A male patient in their mid- to late 60s. A dermoscopic photograph of a skin lesion — 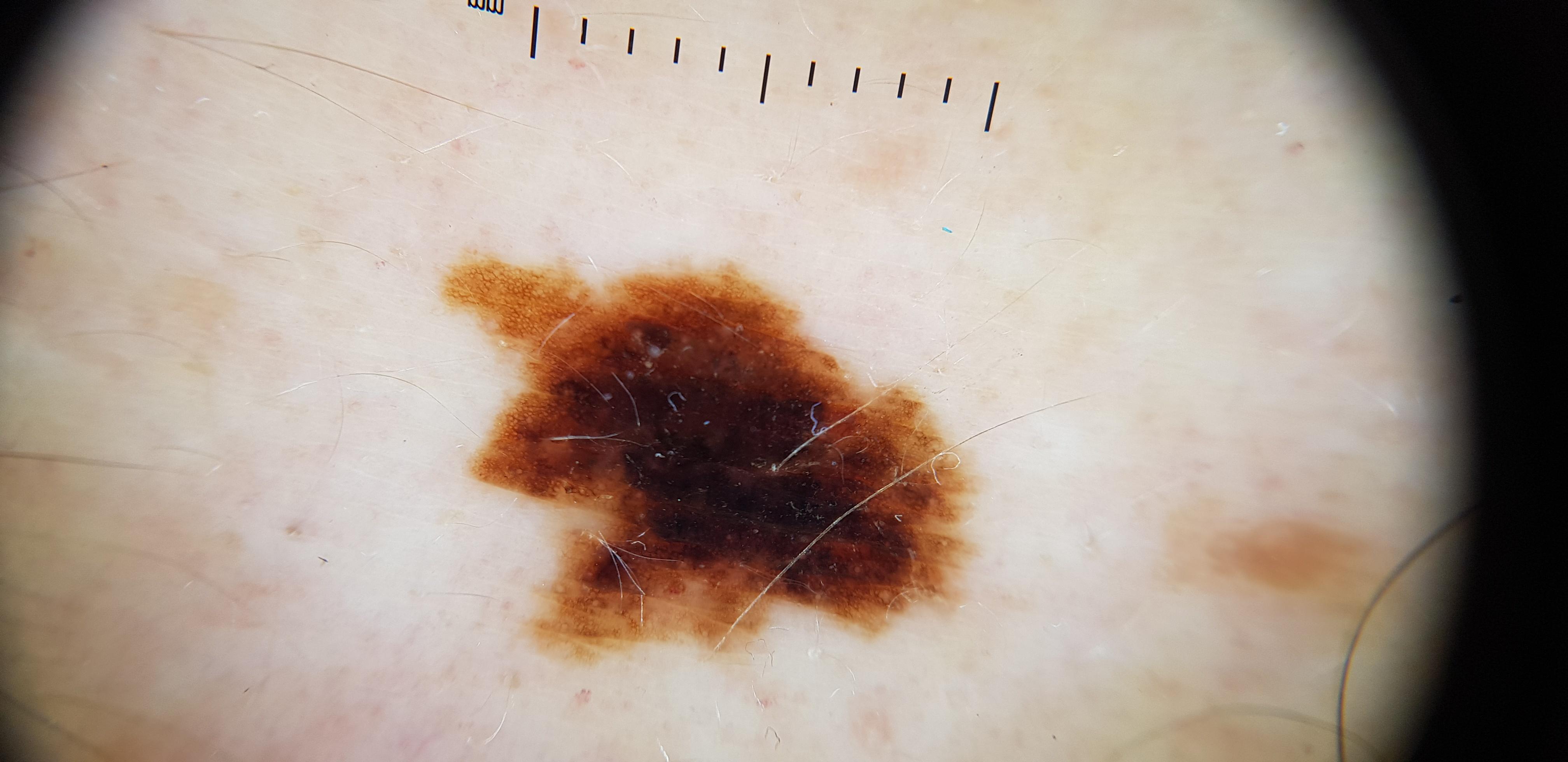The lesion is on the trunk (the posterior trunk). Histopathology confirmed a melanoma.